A female patient, in their mid- to late 50s; a dermoscopic image of a skin lesion — 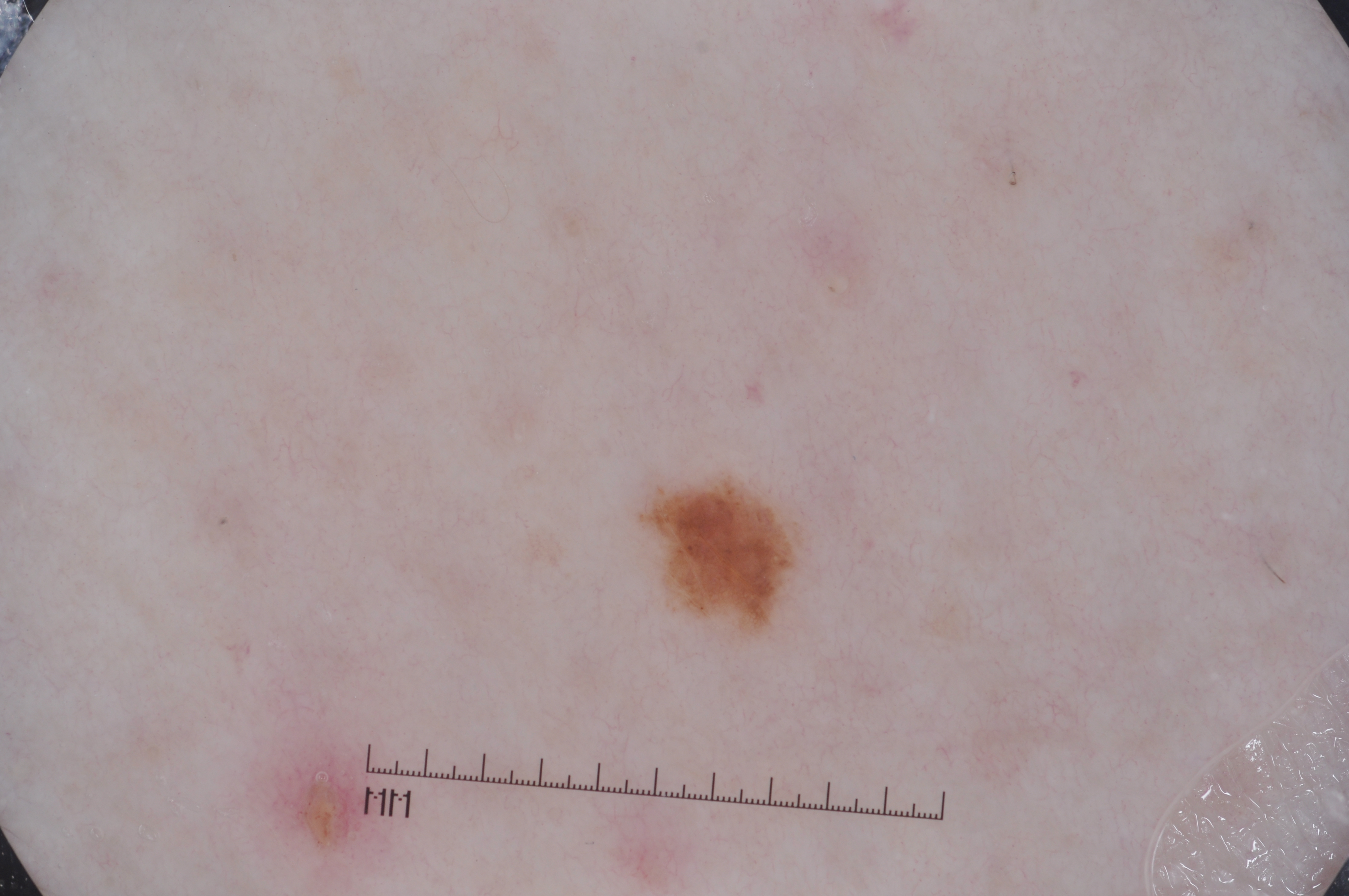  lesion_location:
    bbox_xyxy:
      - 637
      - 475
      - 804
      - 638
  dermoscopic_features:
    present:
      - pigment network
    absent:
      - streaks
      - milia-like cysts
      - negative network
  lesion_extent:
    approx_field_fraction_pct: 1
  diagnosis:
    name: melanocytic nevus
    malignancy: benign
    lineage: melanocytic
    provenance: clinical